Located on the arm and leg · this image was taken at an angle · the contributor is female — 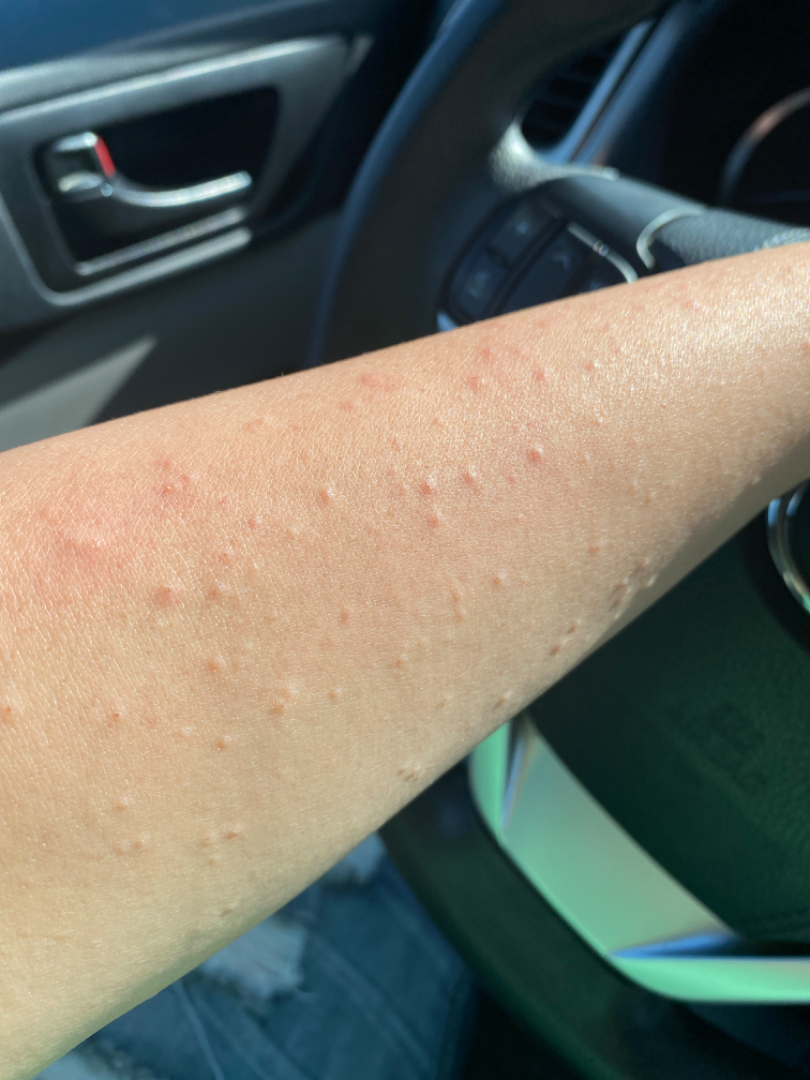onset: less than one week
skin tone: Fitzpatrick skin type II; human graders estimated MST 3–4
self-categorized as: a rash
symptoms: itching
described texture: raised or bumpy
clinical impression: the differential, in no particular order, includes Eczema, Viral dermatological disorders and Hypersensitivity